A female patient, approximately 50 years of age. A dermoscopic image of a skin lesion: 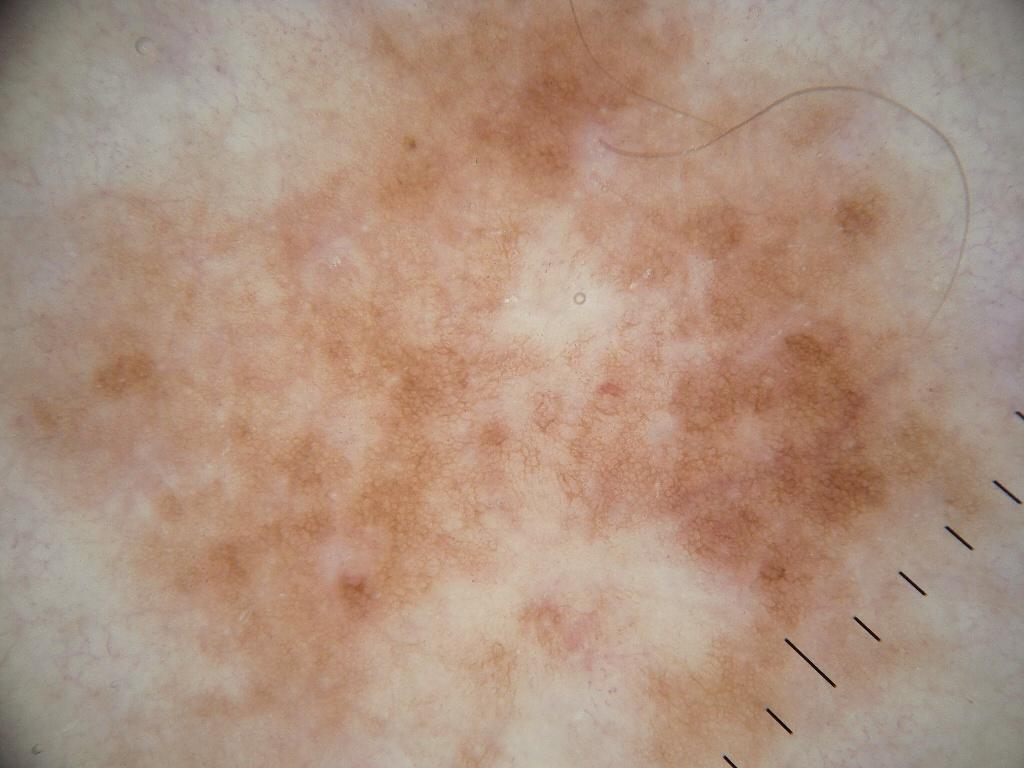Image and clinical context: The lesion stretches across essentially the whole frame. Dermoscopic assessment notes milia-like cysts and pigment network; no streaks, globules, or negative network. Conclusion: The clinical diagnosis was a melanocytic nevus, a benign lesion.